Skin tone: FST II; the patient is male; the patient reported no relevant symptoms from the lesion; the leg is involved; the condition has been present for about one day; texture is reported as raised or bumpy; this image was taken at a distance.
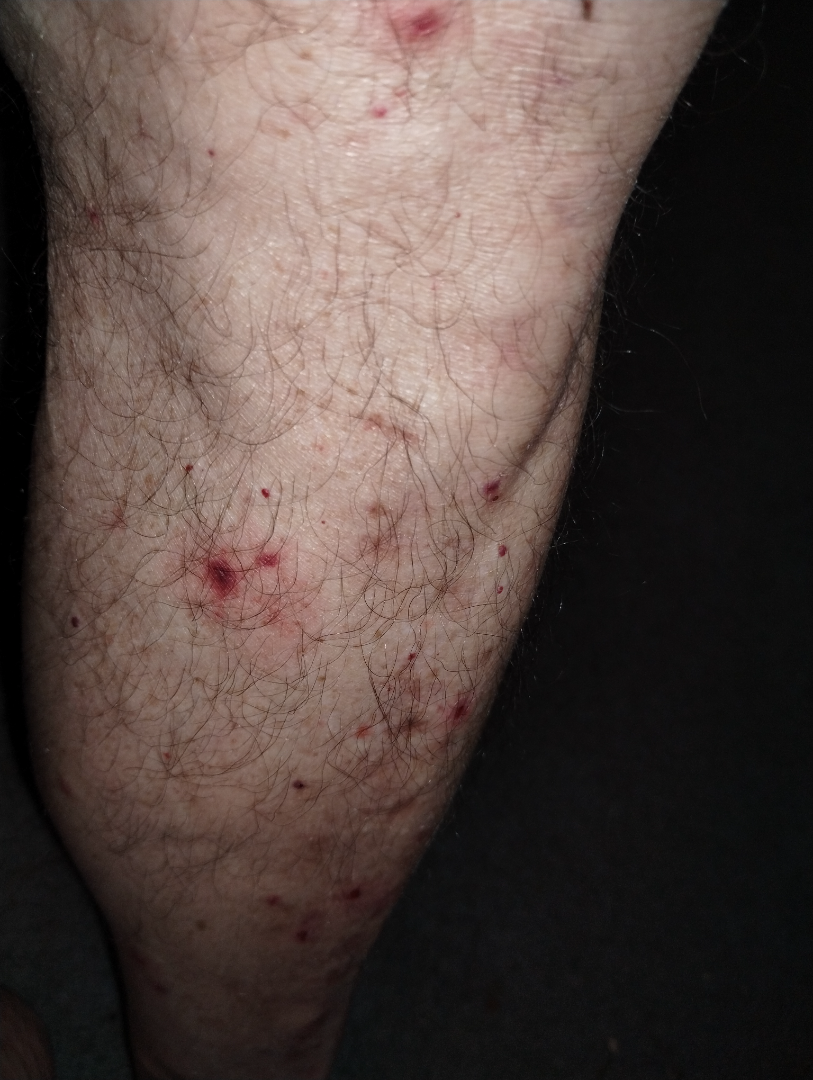Review:
On teledermatology review, Purpura and Folliculitis were considered with similar weight.